This is a close-up image, the contributor is female, the lesion involves the arm: 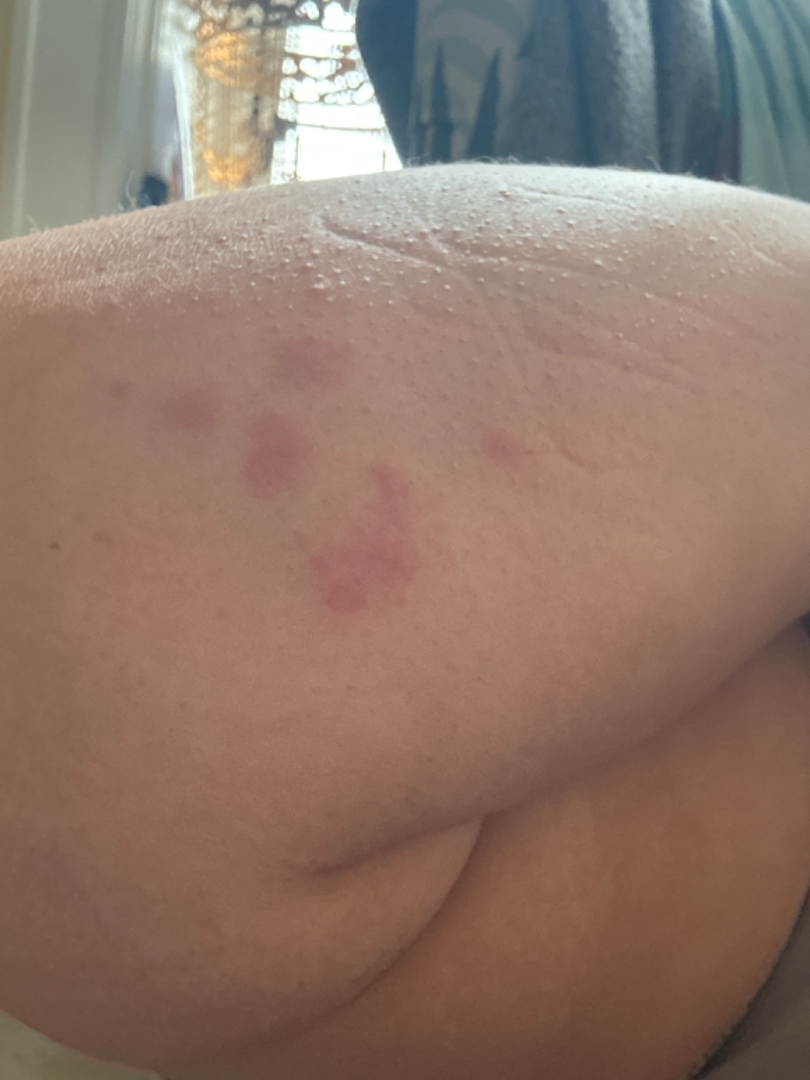Self-reported Fitzpatrick V.
Symptoms reported: enlargement and itching.
On remote dermatologist review, the leading impression is Insect Bite.